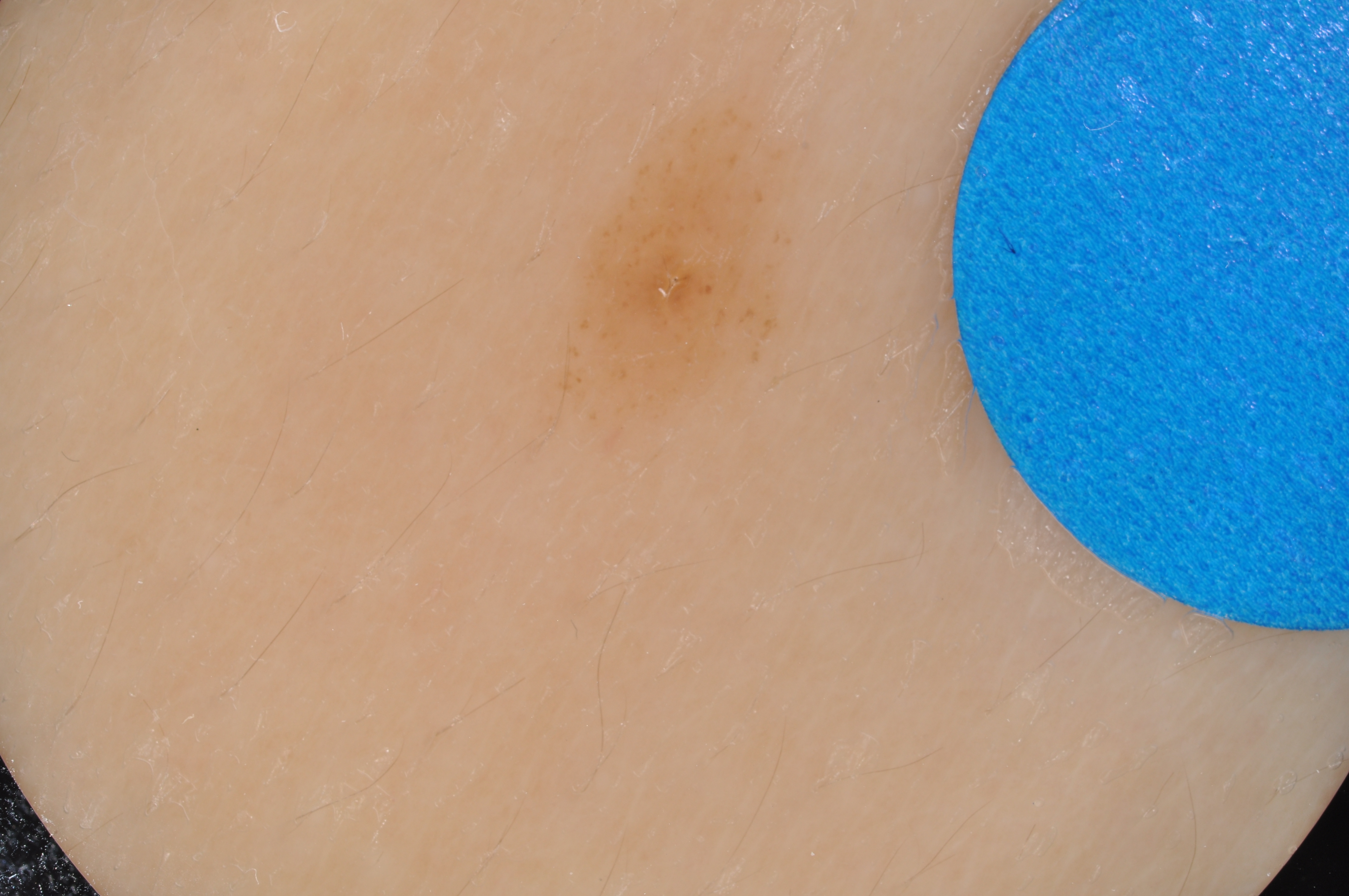patient: male, about 15 years old; image: dermatoscopic image of a skin lesion; absent dermoscopic features: globules, streaks, milia-like cysts, negative network, and pigment network; bounding box: box(538, 82, 836, 452); lesion size: small; diagnosis: a melanocytic nevus.